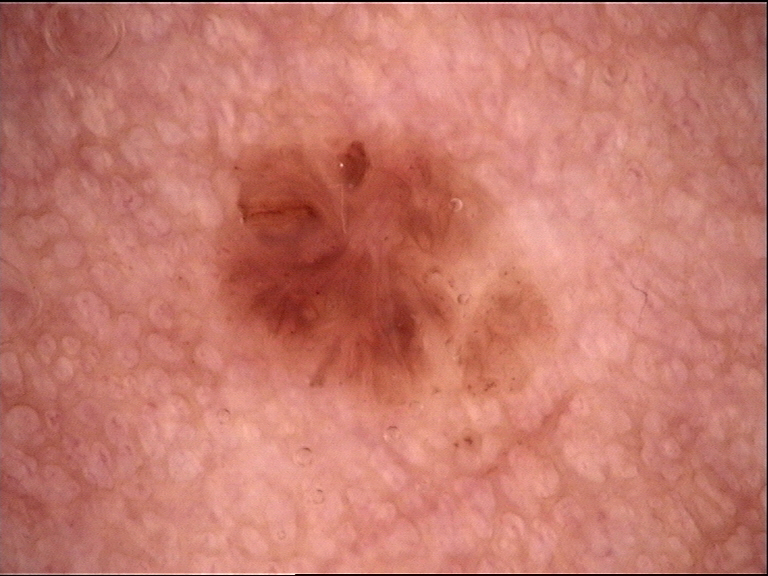{
  "diagnosis": {
    "name": "dermal nevus",
    "code": "db",
    "malignancy": "benign",
    "super_class": "melanocytic",
    "confirmation": "expert consensus"
  }
}